The contributor reports enlargement and itching. The photograph is a close-up of the affected area. The subject is female. Self-categorized by the patient as a nail problem. Texture is reported as raised or bumpy. Located on the arm:
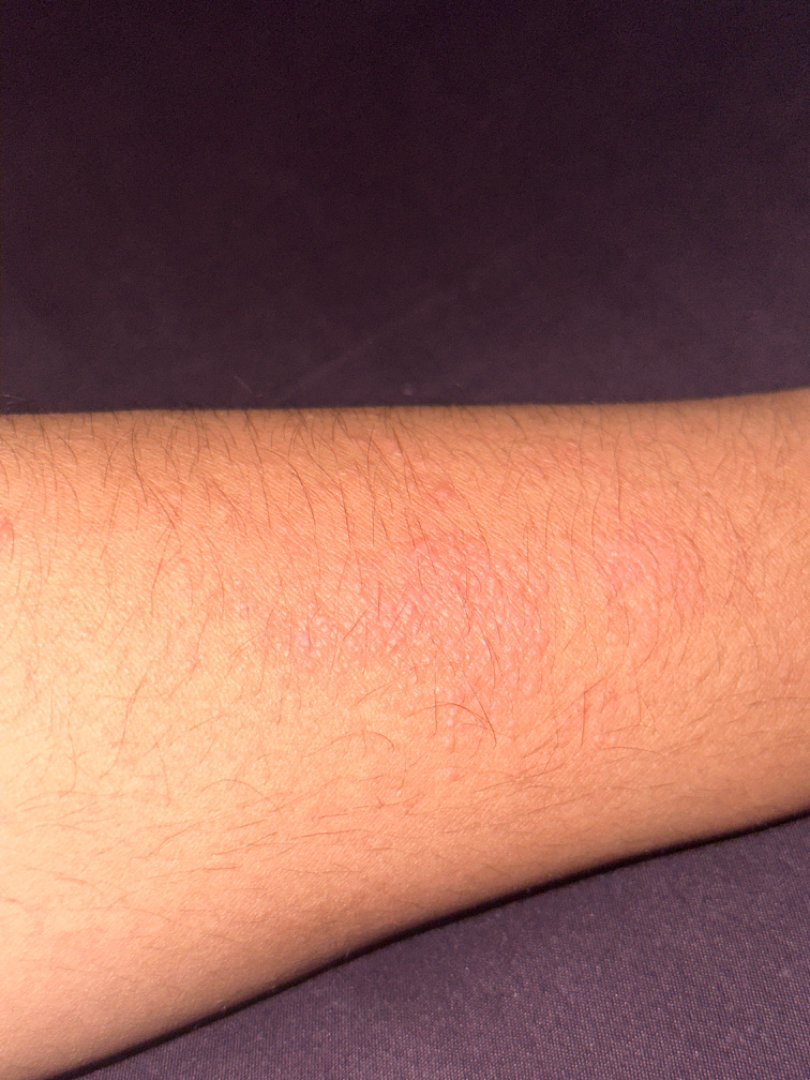The favored diagnosis is Allergic Contact Dermatitis; also raised was Acute and chronic dermatitis; possibly Eczema; less probable is Lichen nitidus.